Lay reviewers estimated MST 2 or 3. The condition has been present for about one day. The patient indicates the lesion is raised or bumpy. The lesion is associated with itching and enlargement. Female subject, age 70–79. No associated systemic symptoms reported. This image was taken at a distance. The patient described the issue as a rash. The affected area is the arm and head or neck:
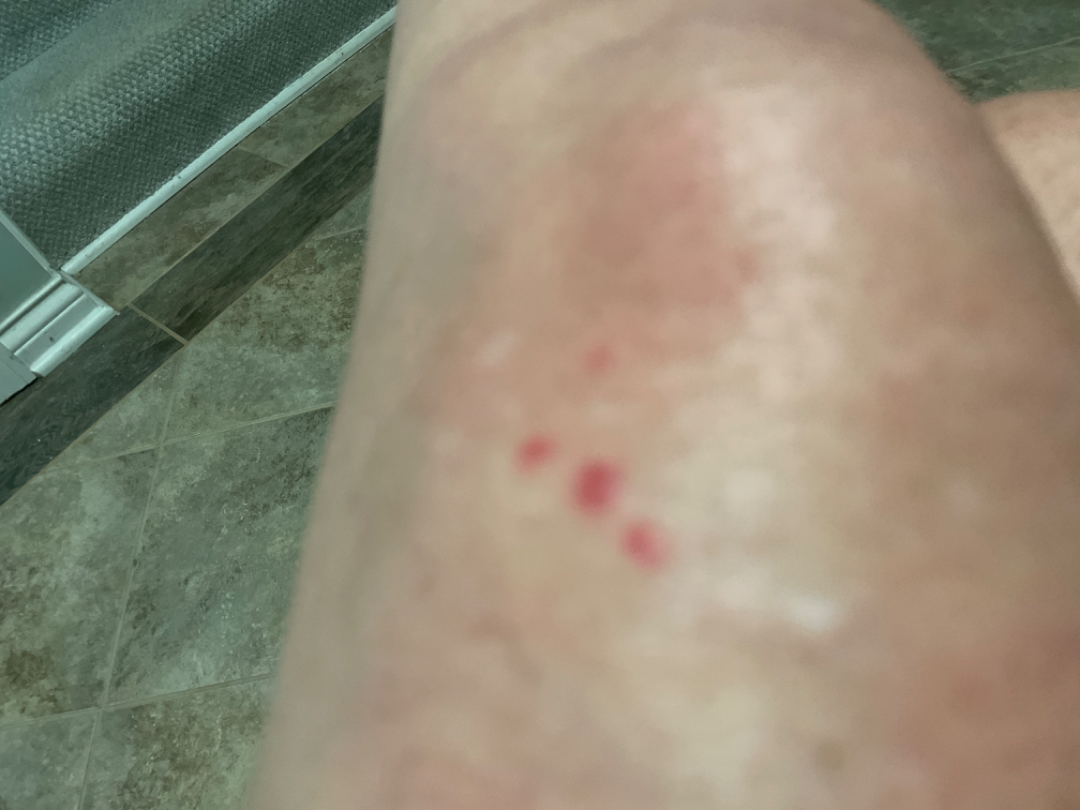• assessment: indeterminate